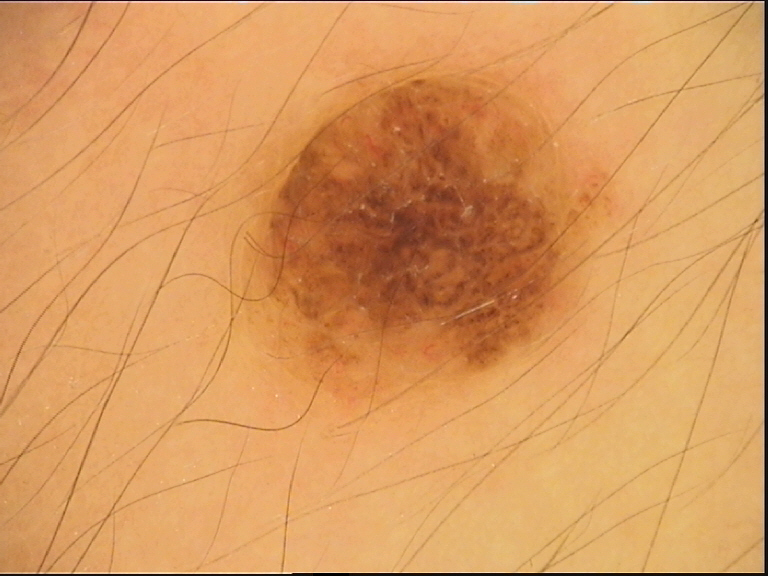image type=dermatoscopy | label=compound nevus (expert consensus).